The affected area is the leg and back of the hand, this image was taken at a distance.
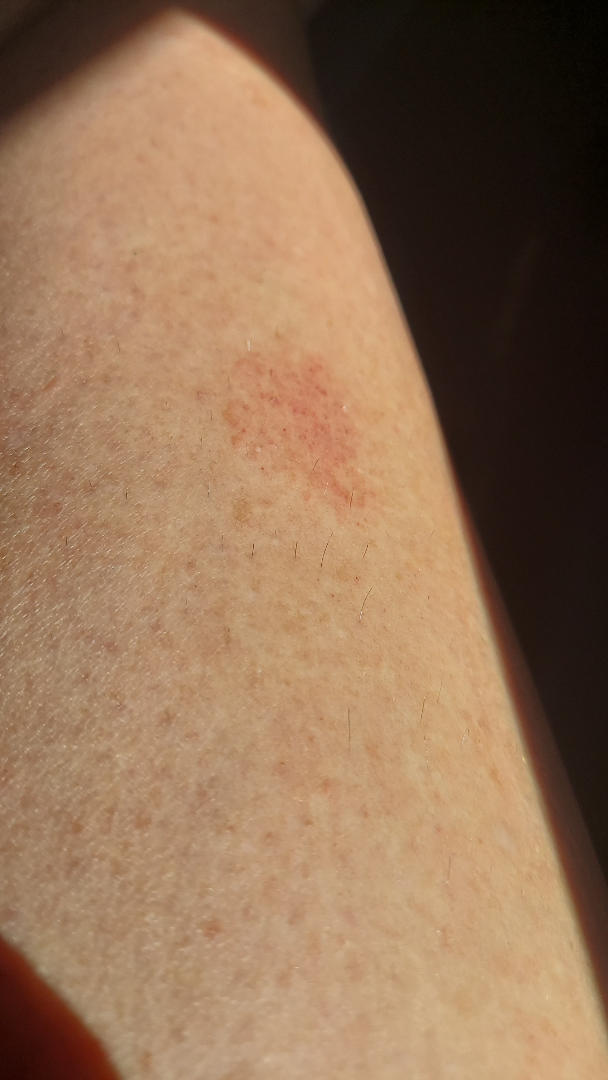The contributor reports the condition has been present for one to four weeks. The contributor reports enlargement. Self-categorized by the patient as a rash. No associated systemic symptoms reported. The contributor reports the lesion is raised or bumpy. Most likely Pigmented purpuric eruption; possibly Tinea; also raised was Eczema.